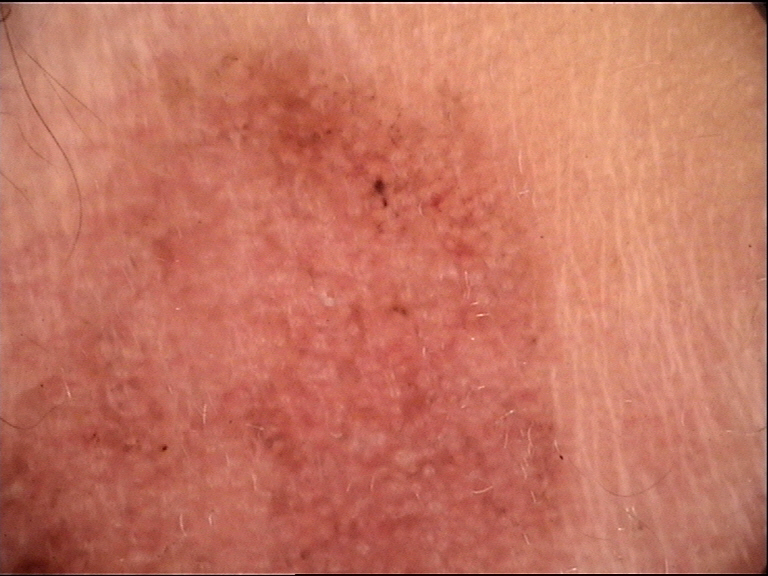Q: What was the diagnostic impression?
A: actinic keratosis (expert consensus)